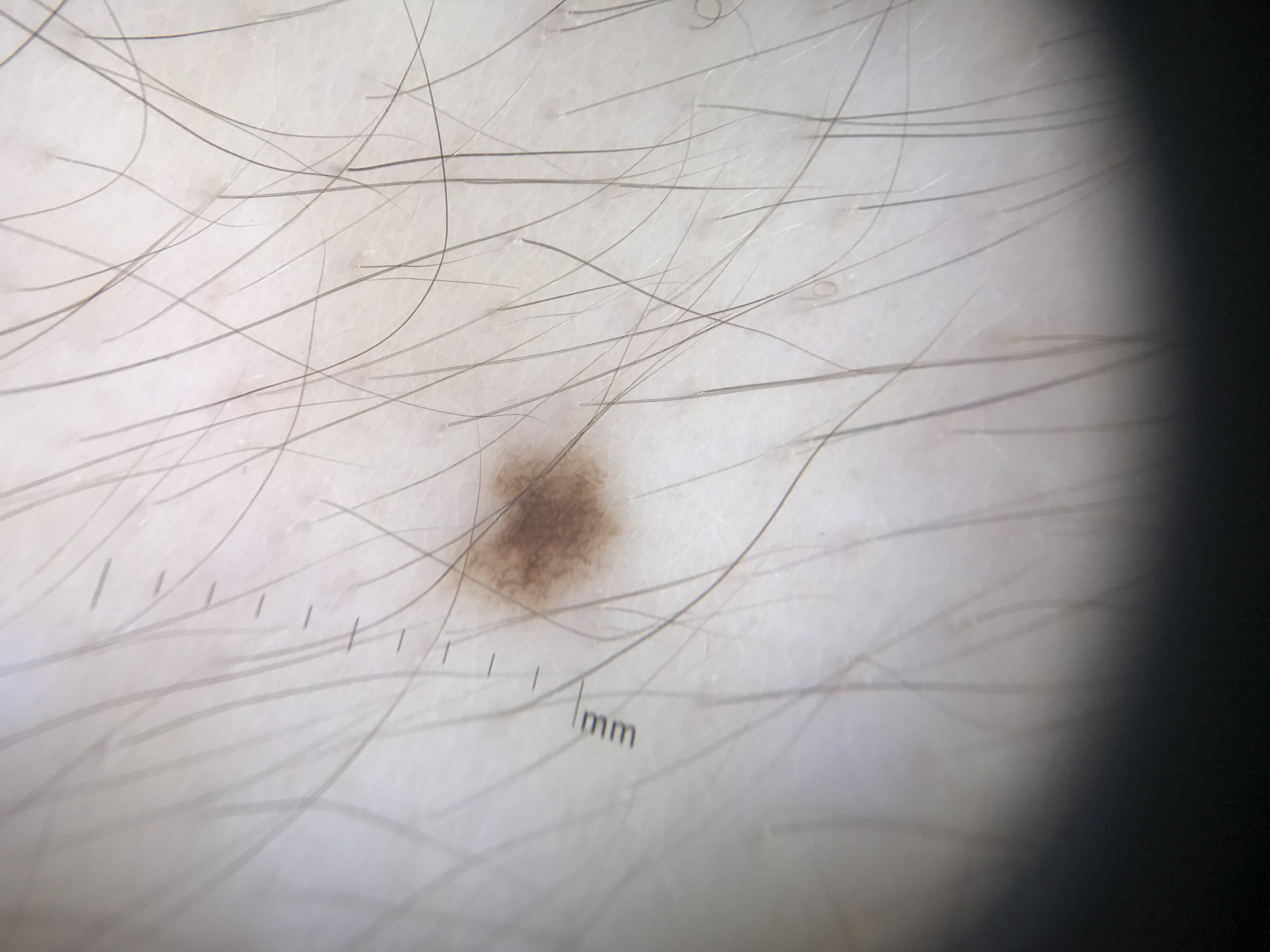– imaging — dermatoscopy
– classification — banal
– label — junctional nevus (expert consensus)